A male subject in their 50s:
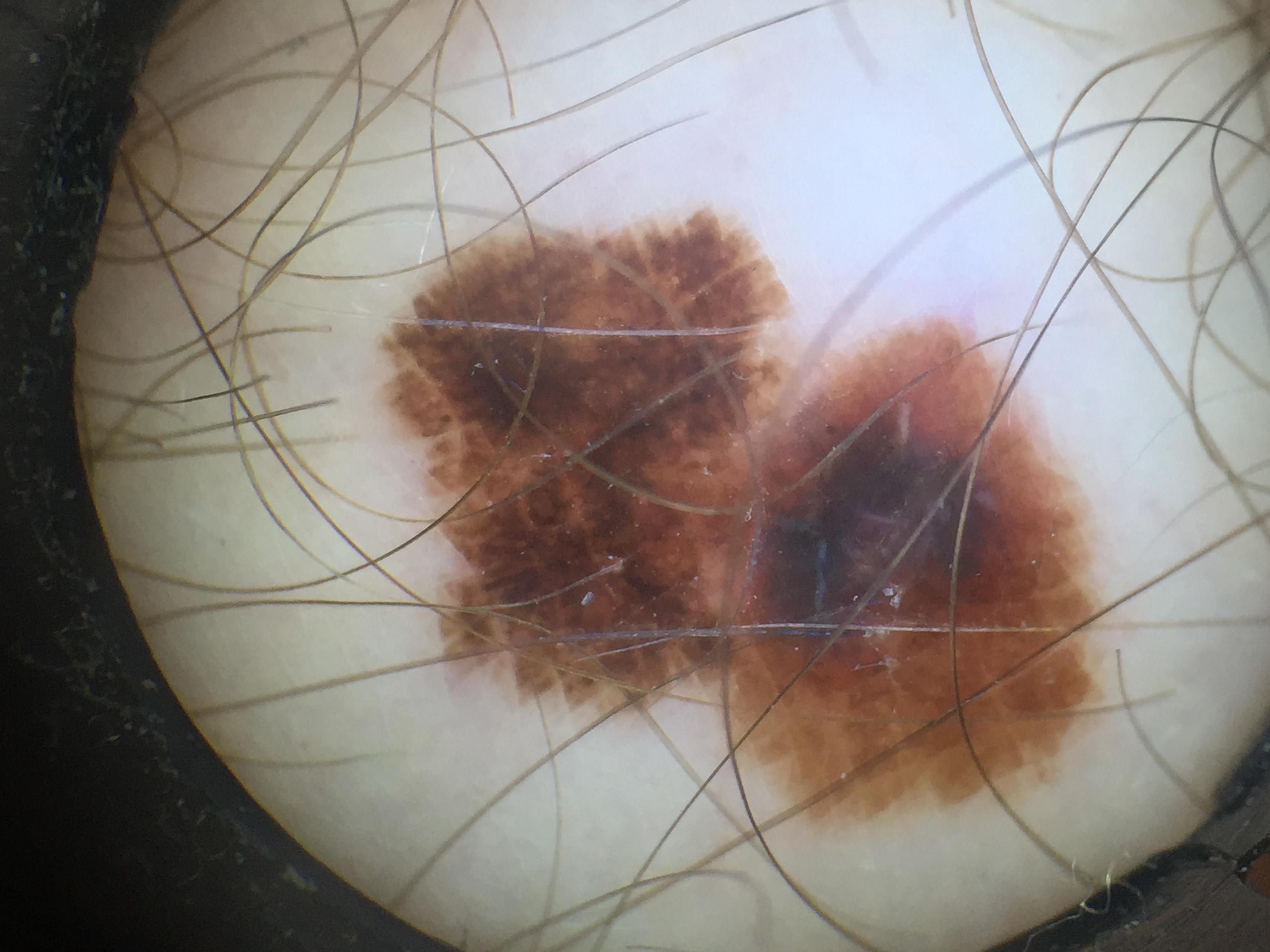{
  "diagnosis": {
    "name": "Melanoma",
    "malignancy": "malignant",
    "confirmation": "histopathology"
  }
}